The affected area is the leg · the contributor is a female aged 30–39 · close-up view:
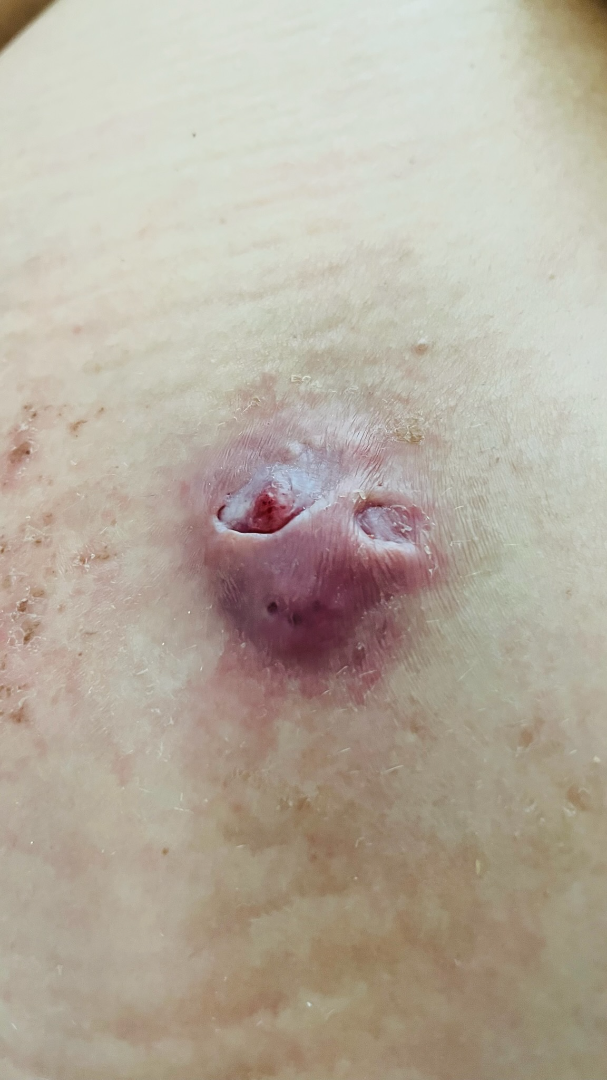{
  "systemic_symptoms": [
    "chills",
    "joint pain",
    "fatigue",
    "shortness of breath"
  ],
  "differential": {
    "Hidradenitis": 1.0
  }
}